The subject is male, this is a close-up image, located on the head or neck — 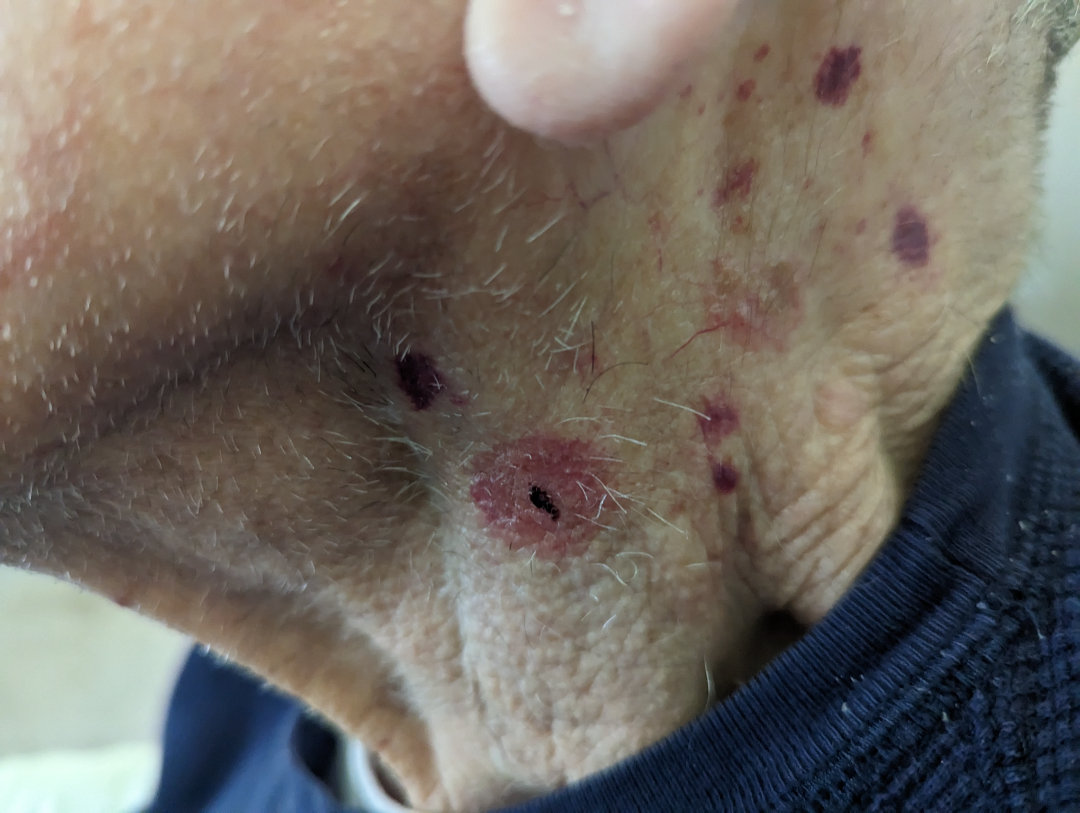<dermatology_case>
  <skin_tone>
    <fitzpatrick>I</fitzpatrick>
    <monk_skin_tone>2, 3</monk_skin_tone>
  </skin_tone>
  <patient_category>a rash</patient_category>
  <texture>rough or flaky, raised or bumpy</texture>
  <symptoms>bothersome appearance, burning, enlargement</symptoms>
  <systemic_symptoms>mouth sores</systemic_symptoms>
  <duration>one to three months</duration>
  <differential>
    <leading>Purpura</leading>
    <considered>ecchymoses</considered>
  </differential>
</dermatology_case>